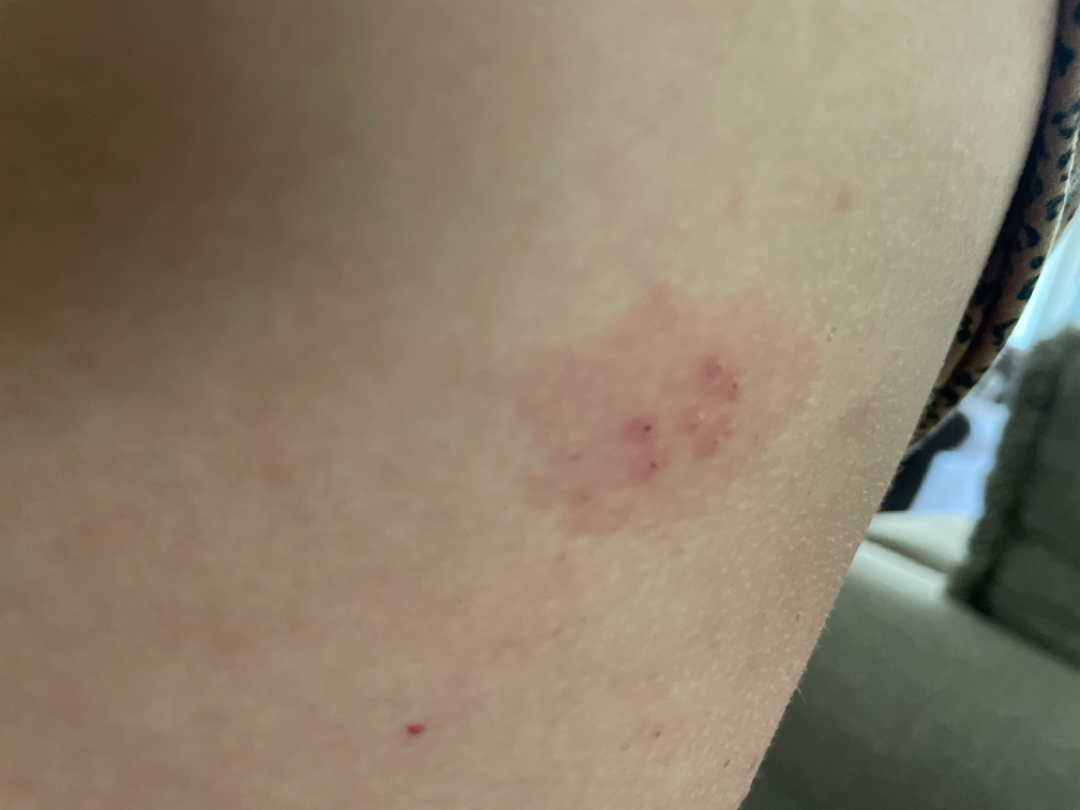{"duration": "less than one week", "shot_type": "at an angle", "texture": "raised or bumpy", "patient": "female, age 40–49", "body_site": "back of the torso", "symptoms": ["burning", "pain", "itching"], "patient_category": "skin that appeared healthy to them", "differential": {"leading": ["Molluscum Contagiosum"], "considered": ["Herpes Simplex"], "unlikely": ["Impetigo", "Allergic Contact Dermatitis"]}}